A female subject aged approximately 55 · dermoscopy of a skin lesion: 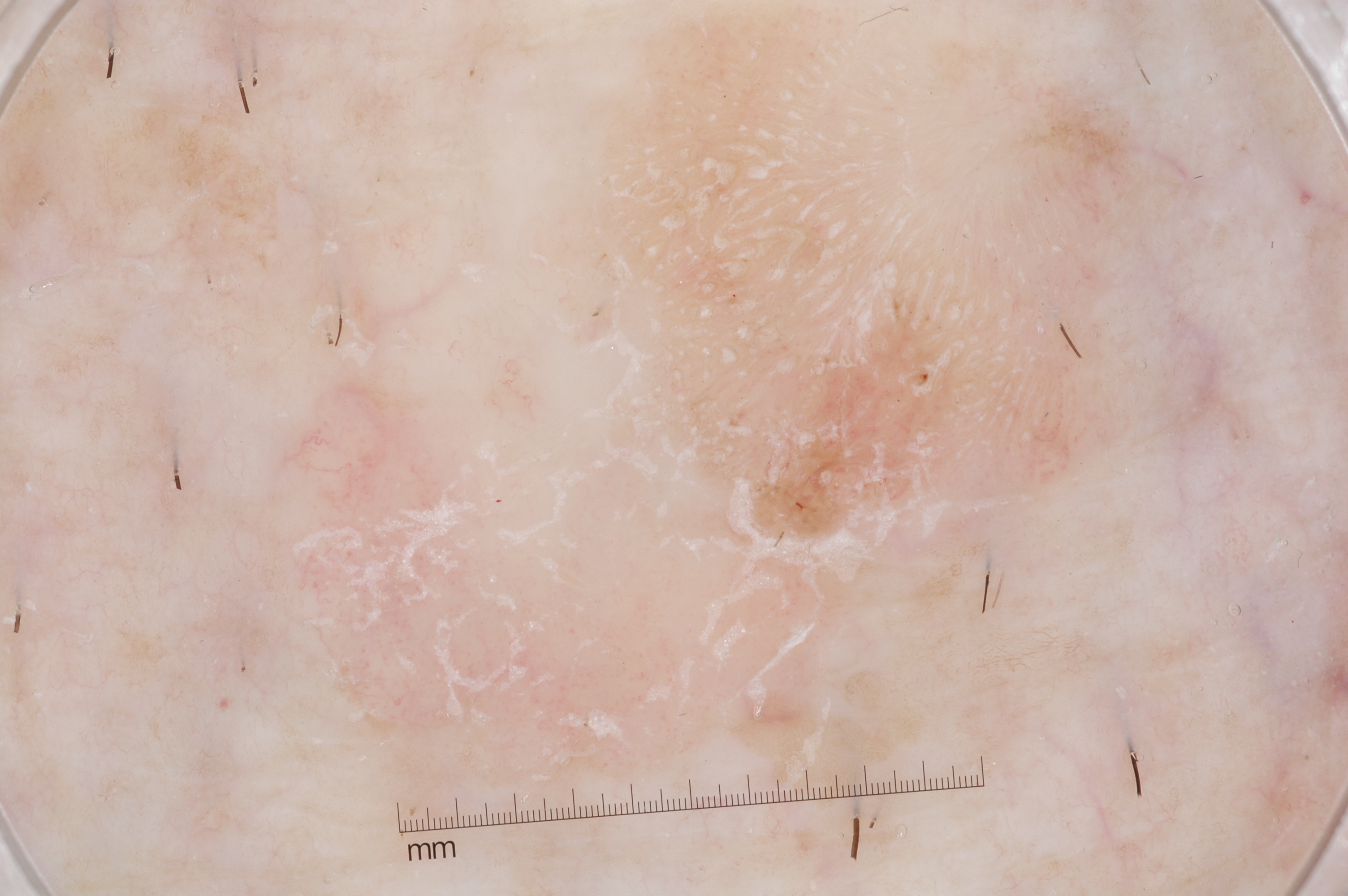The lesion is bounded by [223, 6, 1225, 850]. Dermoscopic examination shows no milia-like cysts, negative network, pigment network, or streaks. The lesion occupies roughly 63% of the field. Expert review diagnosed this as a seborrheic keratosis, a benign lesion.